A dermoscopic close-up of a skin lesion:
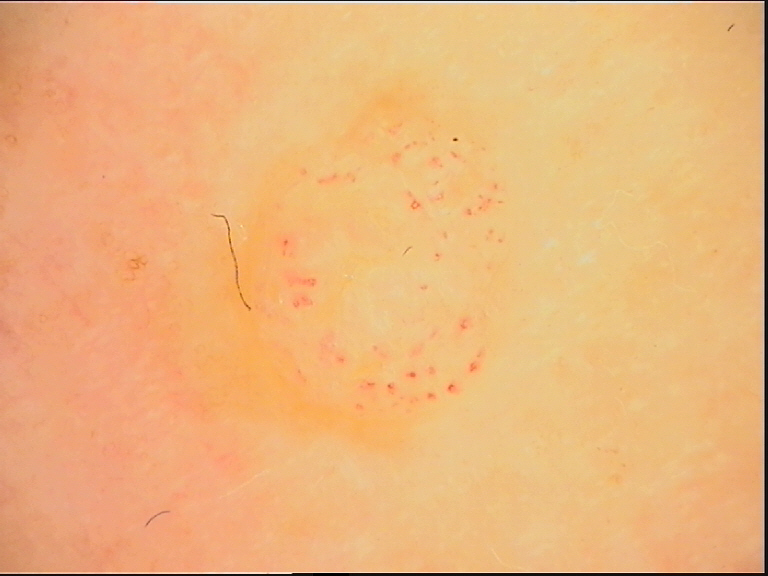Findings:
- category — banal
- diagnostic label — dermal nevus (expert consensus)